The lesion involves the arm. The contributor is female. The photo was captured at a distance.
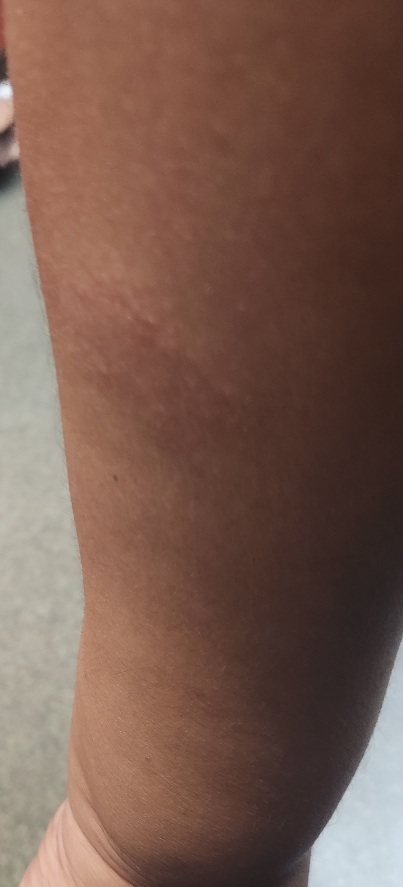assessment: Eczema (leading); Contact dermatitis (possible); Tinea (less likely).